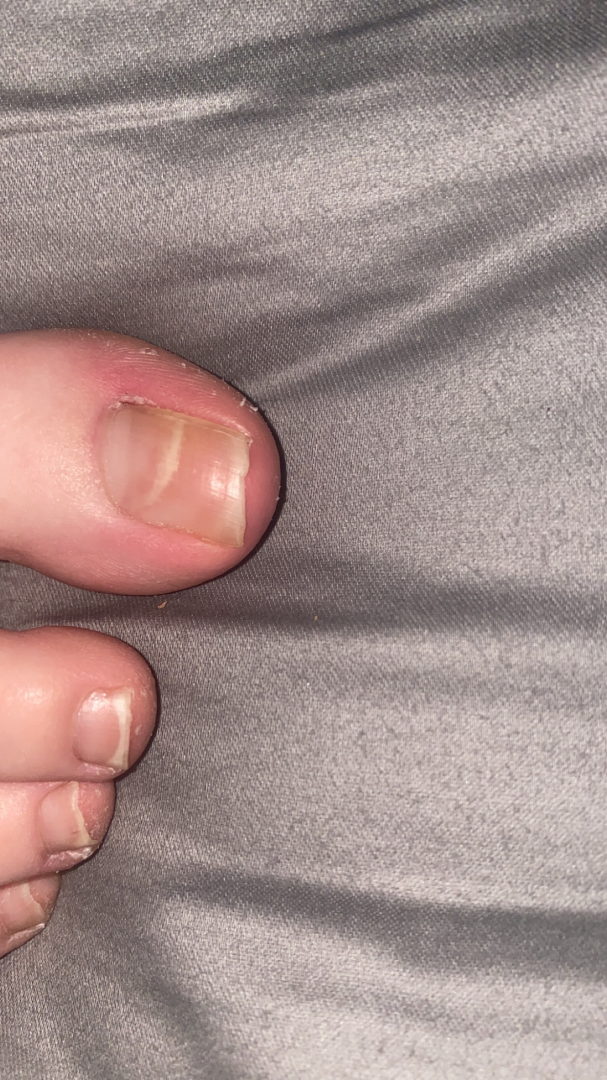Clinical context: A close-up photograph. Symptoms reported: darkening and bothersome appearance. The patient is 18–29, female. The contributor reports the condition has been present for one to three months. Located on the top or side of the foot. The patient considered this a nail problem. Assessment: The reviewing dermatologist's impression was: most likely Leukonychia; with consideration of Muehrcke lines; the differential also includes Nail dystrophy.